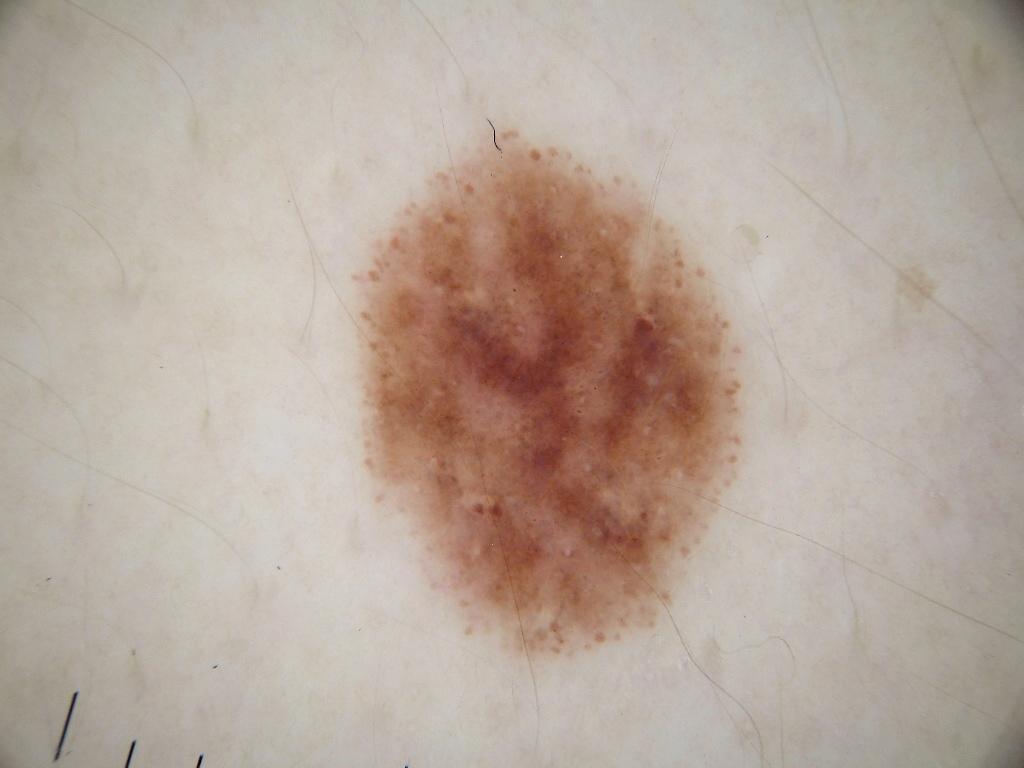Case summary:
A male subject roughly 20 years of age. A dermoscopic image of a skin lesion. On dermoscopy, the lesion shows globules, with no streaks, negative network, milia-like cysts, or pigment network. The lesion is bounded by 351 122 748 668.
Impression:
Expert review diagnosed this as a melanocytic nevus.